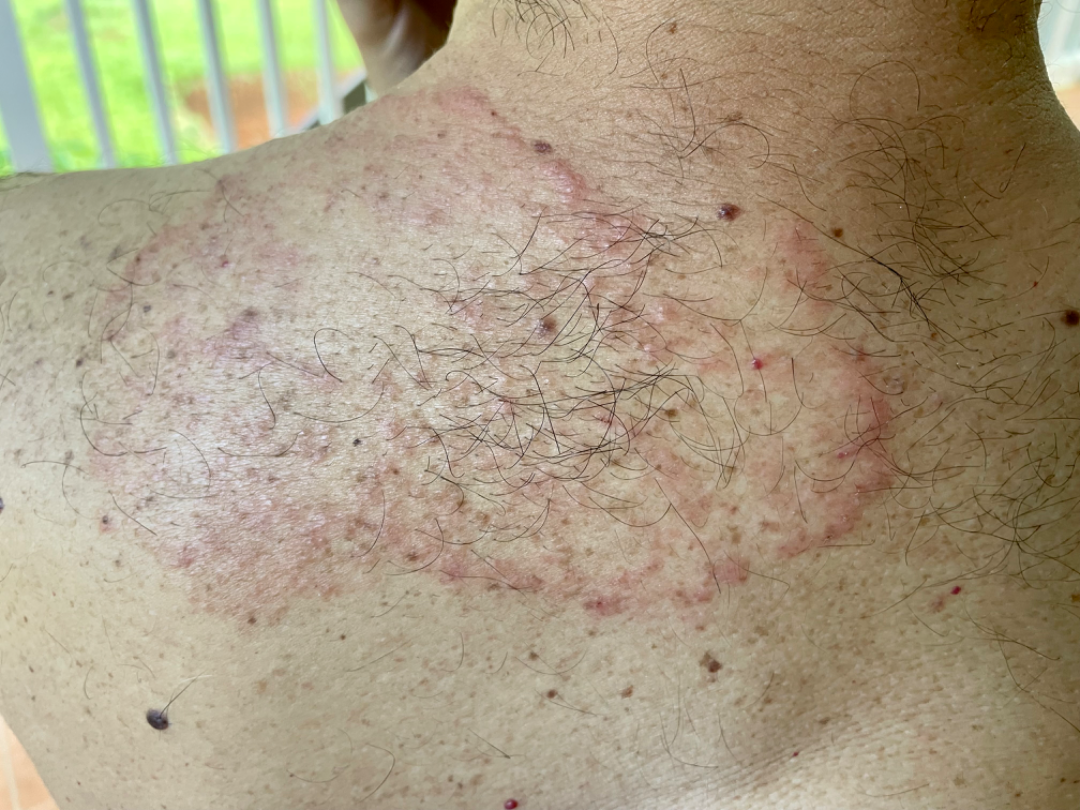– assessment — the impression on review was Tinea